A dermatoscopic image of a skin lesion.
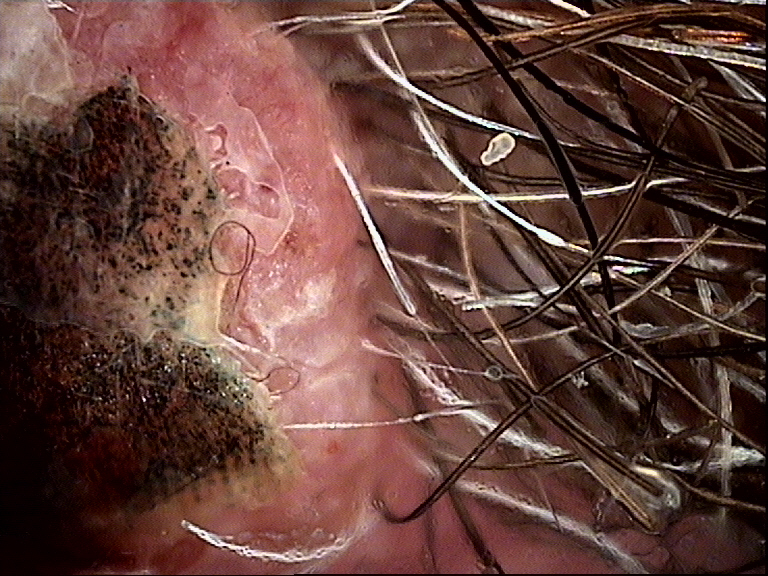Findings:
• diagnostic label · squamous cell carcinoma (biopsy-proven)